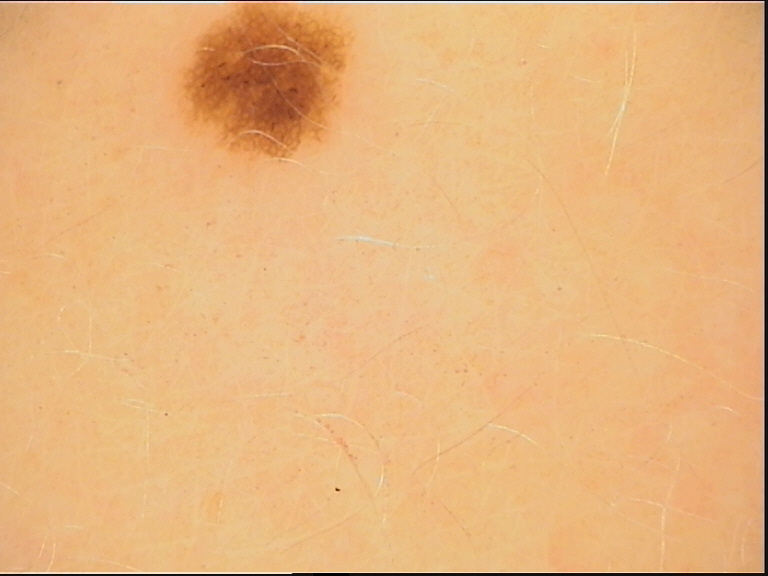diagnostic label=dysplastic junctional nevus (expert consensus).